The photo was captured at a distance; the subject is a male aged 18–29; located on the sole of the foot and top or side of the foot.
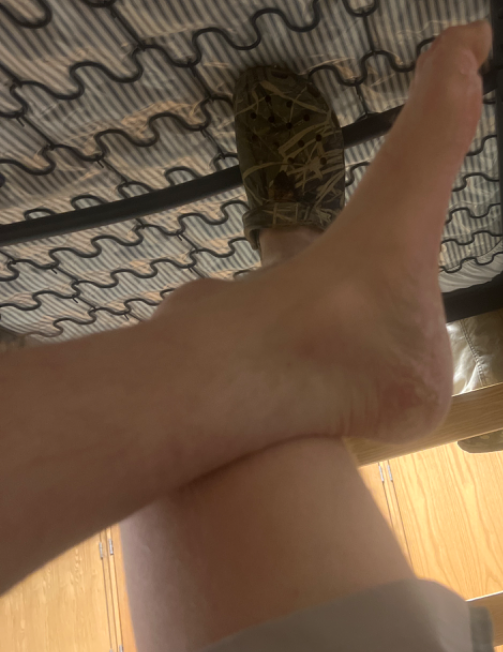| feature | finding |
|---|---|
| assessment | ungradable on photographic review |